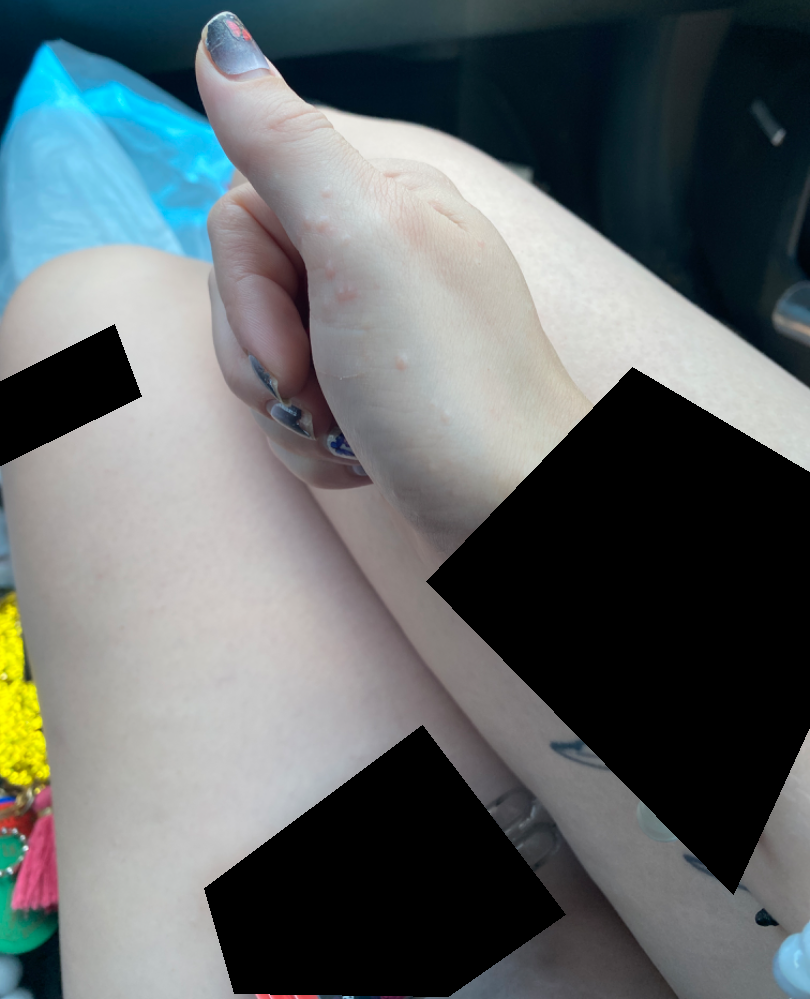  differential:
    tied_lead:
      - Verruca vulgaris
      - Molluscum Contagiosum
    unlikely:
      - Acrokeratosis verruciformis